Texture is reported as raised or bumpy and fluid-filled, an image taken at a distance, the patient described the issue as a rash, the lesion involves the arm, human graders estimated Monk skin tone scale 3.
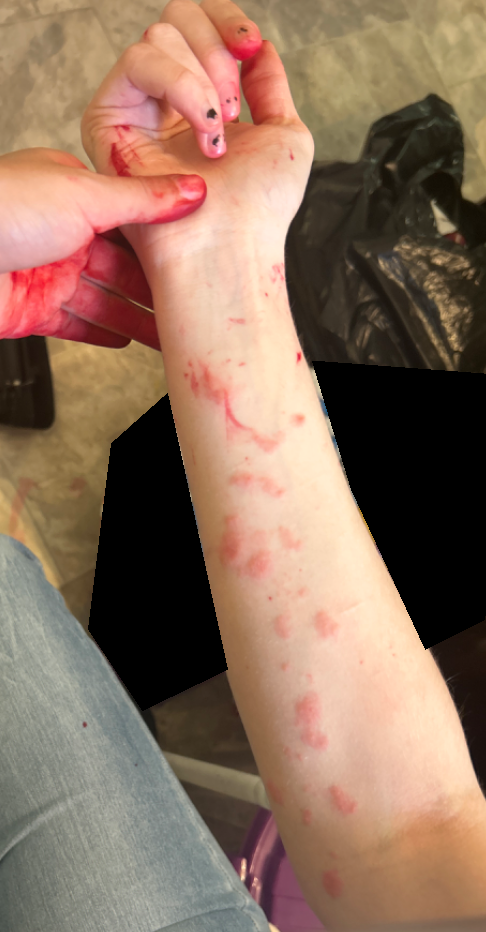The reviewing dermatologist's impression was: most consistent with Acute dermatitis, NOS.